A clinical overview photograph of a skin lesion · the patient was assessed as skin type II:
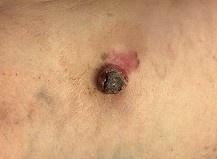The lesion is located on a lower extremity. On biopsy, the diagnosis was a melanoma.